A clinical photograph showing a skin lesion. The chart notes prior malignancy (patient or family): 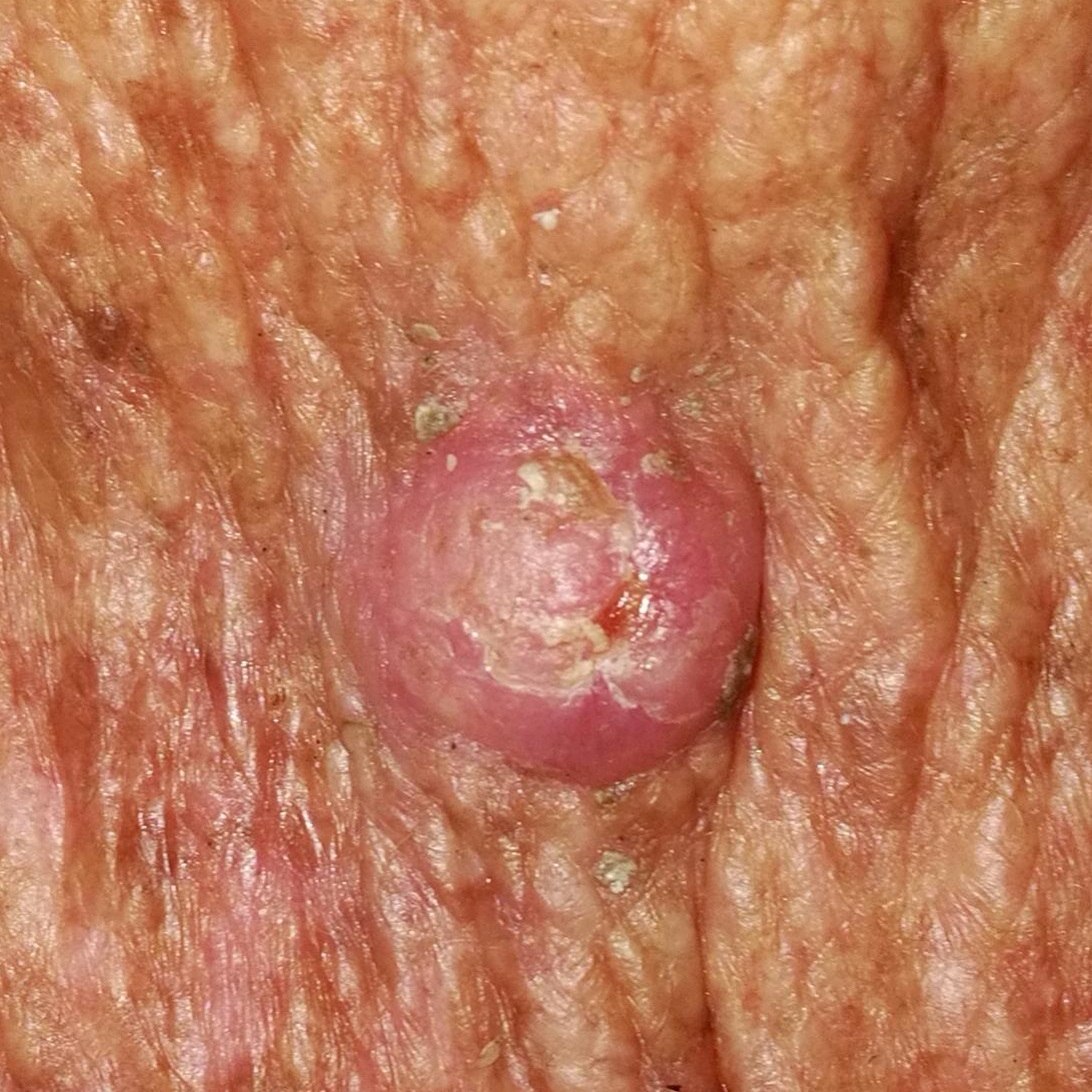Clinical context:
The lesion is located on the chest. The patient describes that the lesion hurts, is elevated, and itches, but has not changed.
Conclusion:
Biopsy-confirmed as a squamous cell carcinoma.